A dermatoscopic image of a skin lesion.
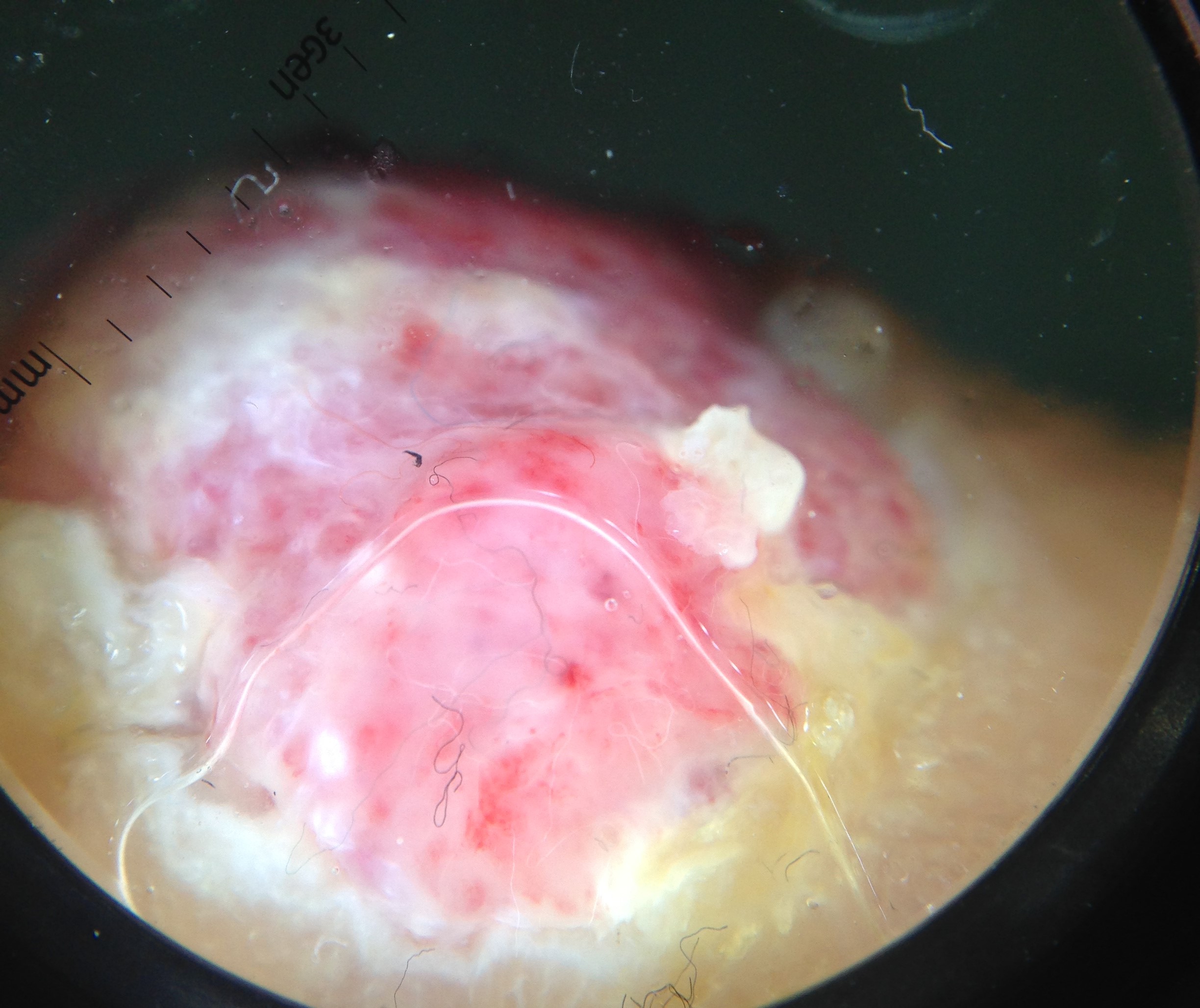Conclusion:
Histopathologically confirmed as a malignancy — an acral nodular melanoma.